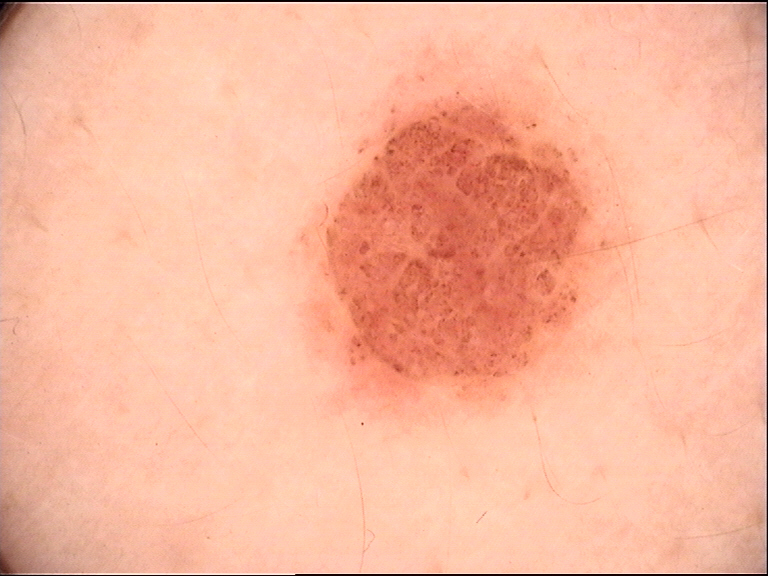classification: banal, diagnosis: dermal nevus (expert consensus).